Female subject, age 18–29; the affected area is the front of the torso and back of the torso; this image was taken at a distance — 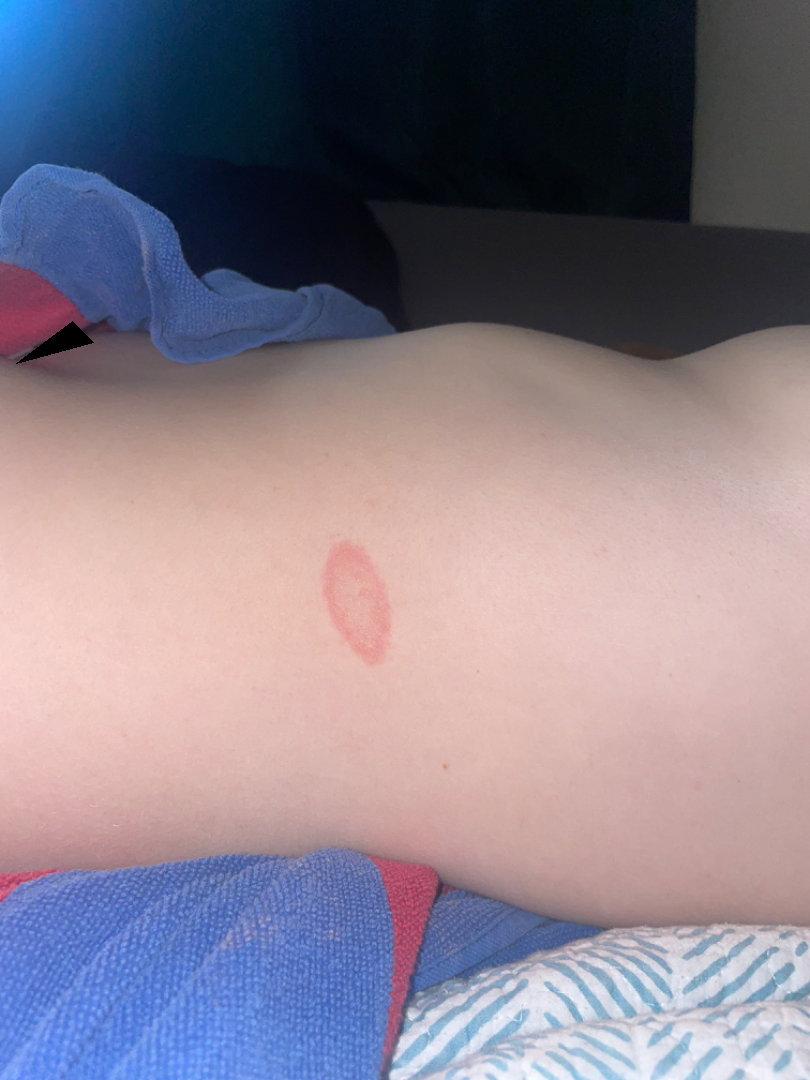{"differential": {"leading": ["Pityriasis rosea"], "unlikely": ["Erythema annulare centrifugum", "Tinea", "Granuloma annulare"]}}